The lesion is described as raised or bumpy; the patient considered this a growth or mole; a close-up photograph; the patient is 40–49, male; reported duration is three to twelve months; located on the back of the hand — 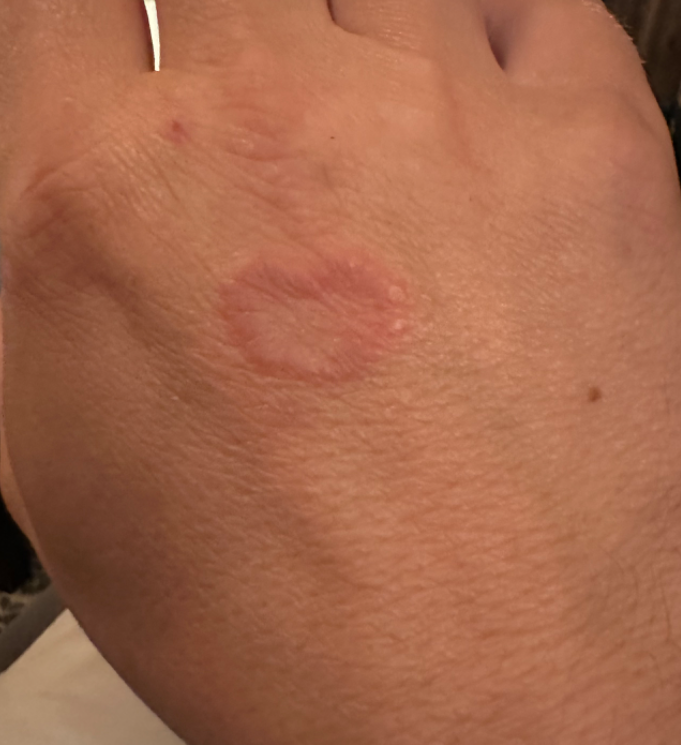On photographic review: the impression on review was Granuloma annulare.